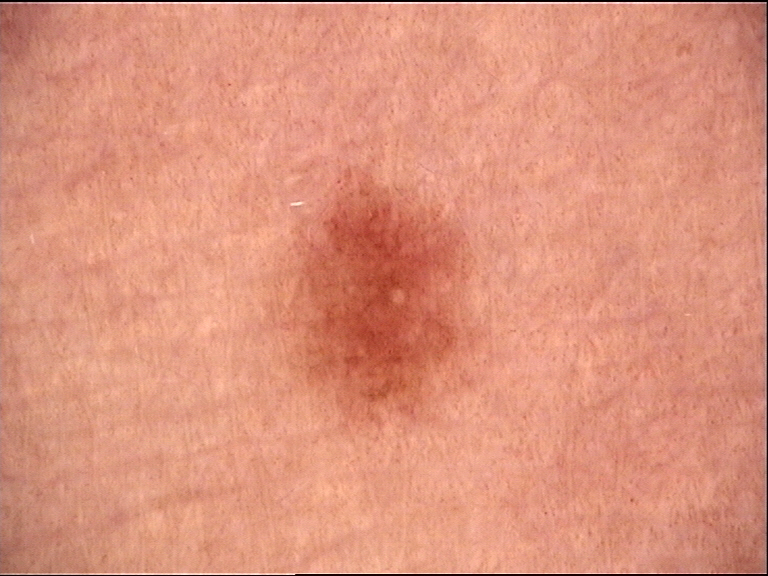Impression: Labeled as a dysplastic junctional nevus.